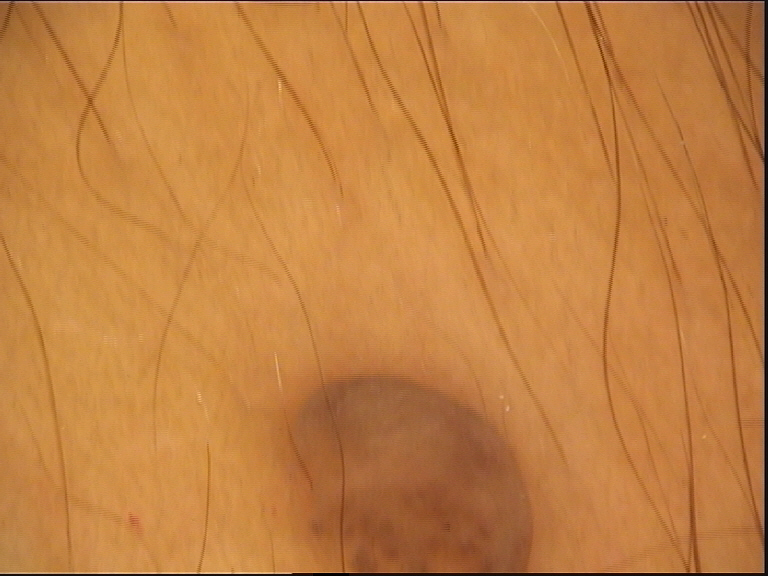Summary: A dermoscopic photograph of a skin lesion. Conclusion: Classified as a banal lesion — a dermal nevus.